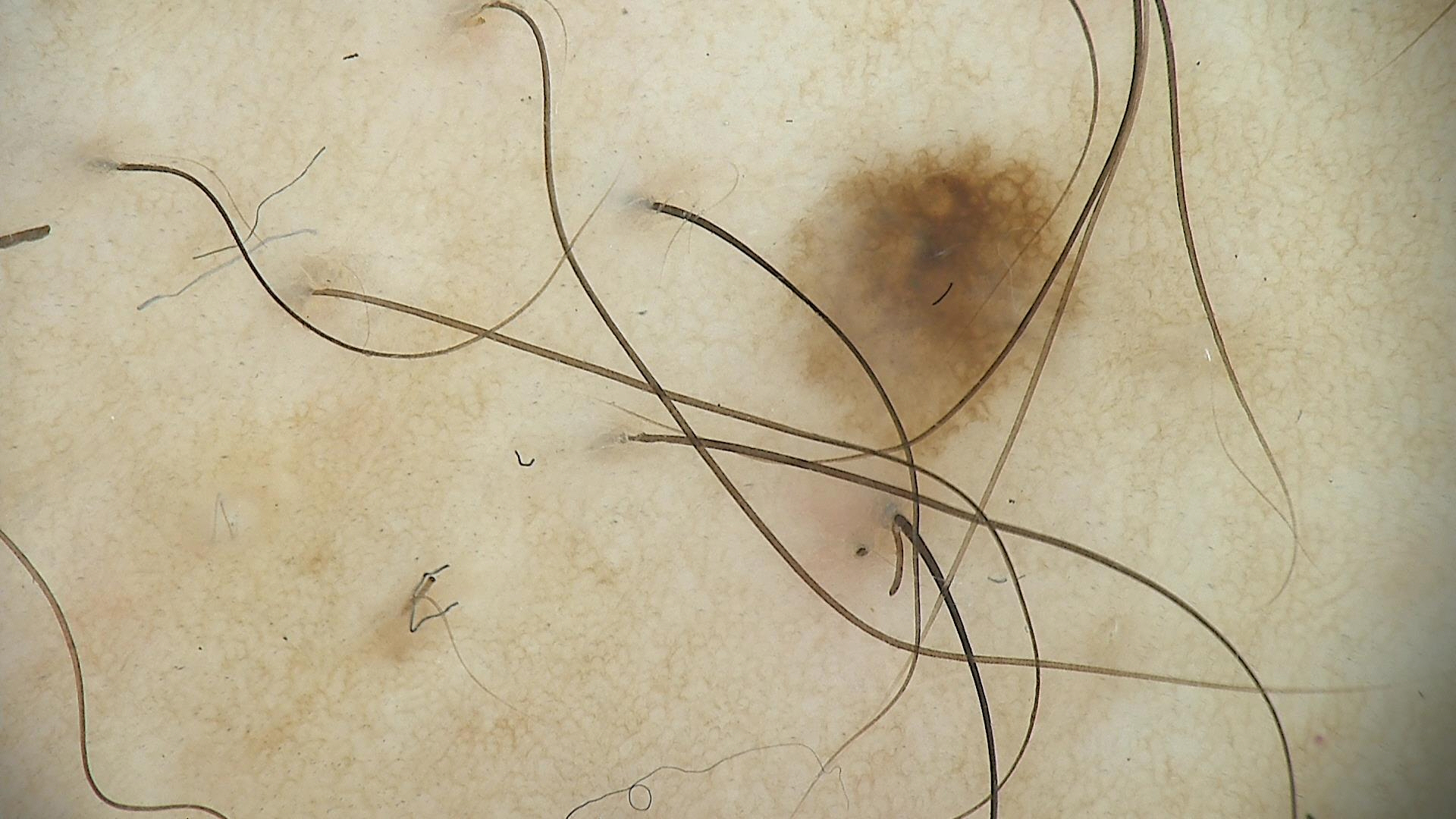Consistent with a dysplastic compound nevus.